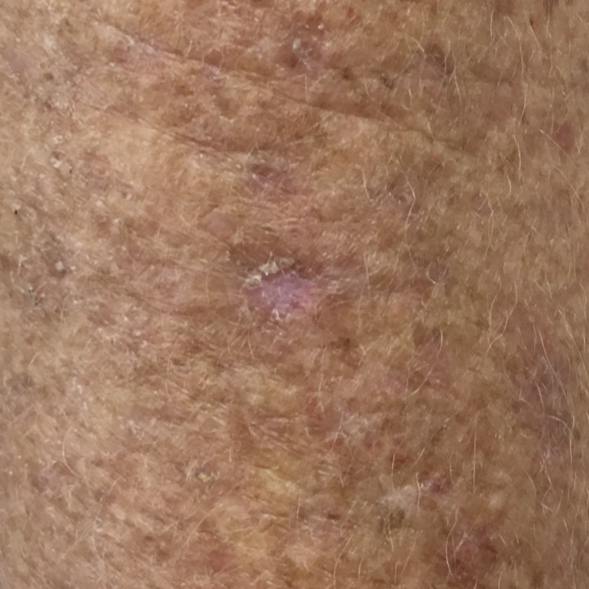Notes:
* image — clinical photograph
* subject — age 60
* body site — a forearm
* patient-reported symptoms — no change in appearance, no growth
* diagnostic label — actinic keratosis (clinical consensus)